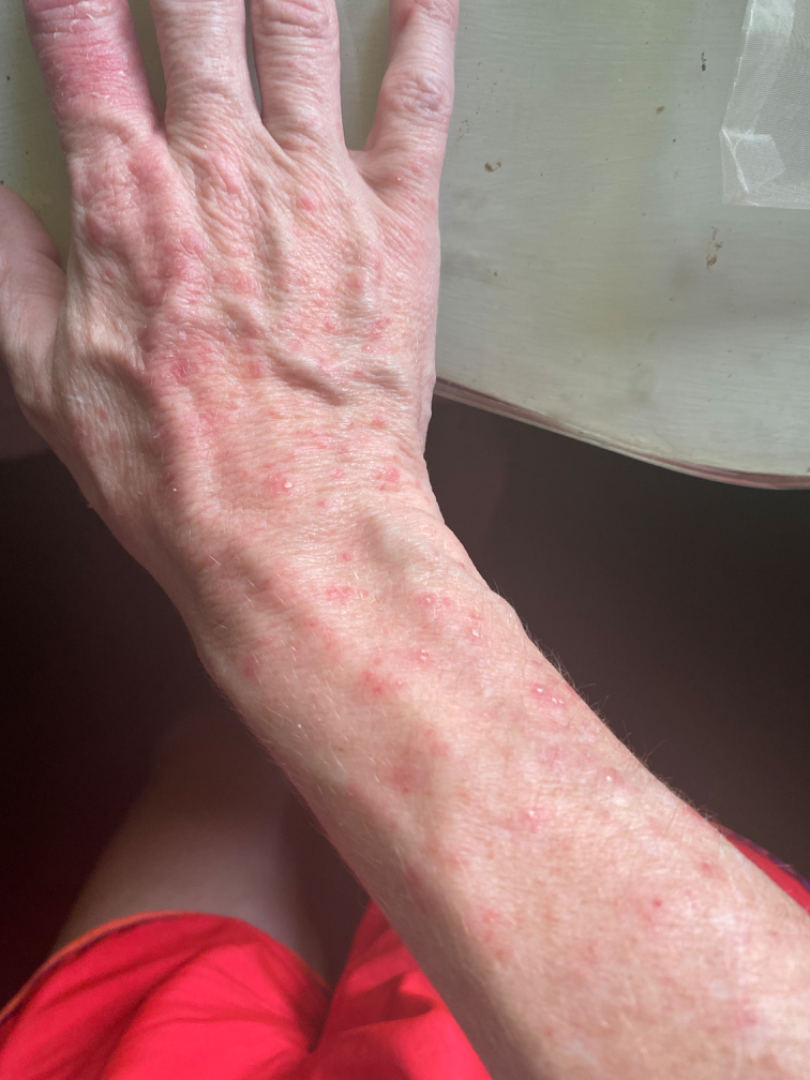{
  "differential": {
    "tied_lead": [
      "Scabies",
      "Psoriasis",
      "Eczema"
    ]
  }
}